A dermatoscopic image of a skin lesion; the patient says their skin reddens with sun exposure; the patient reports a personal history of skin cancer, a personal history of cancer, and no sunbed use; a male patient aged 76; the patient describes having few moles overall — 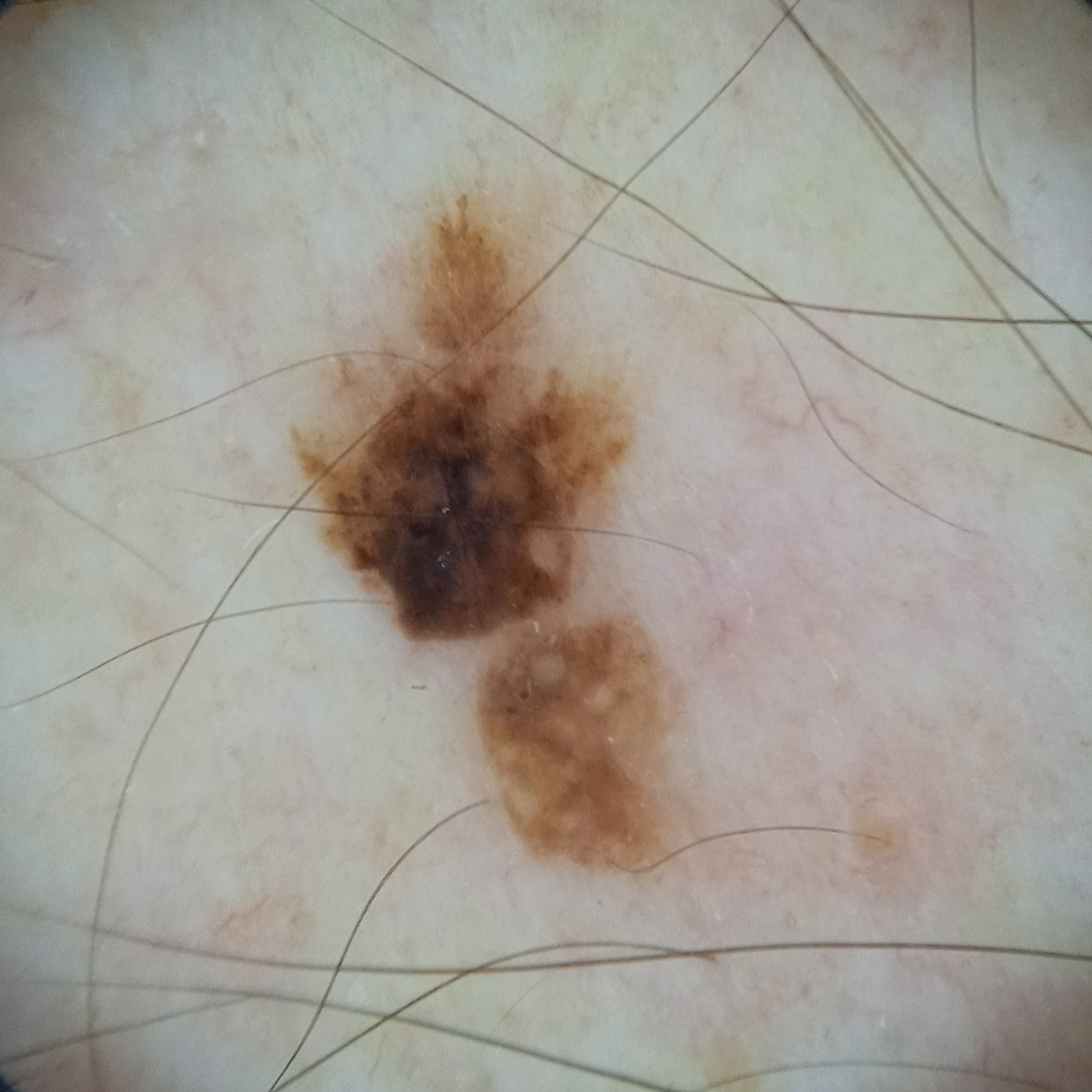{
  "lesion_location": "the back",
  "lesion_size": {
    "diameter_mm": 7.8
  },
  "diagnosis": {
    "name": "seborrheic keratosis",
    "malignancy": "benign",
    "certainty": "moderate"
  }
}